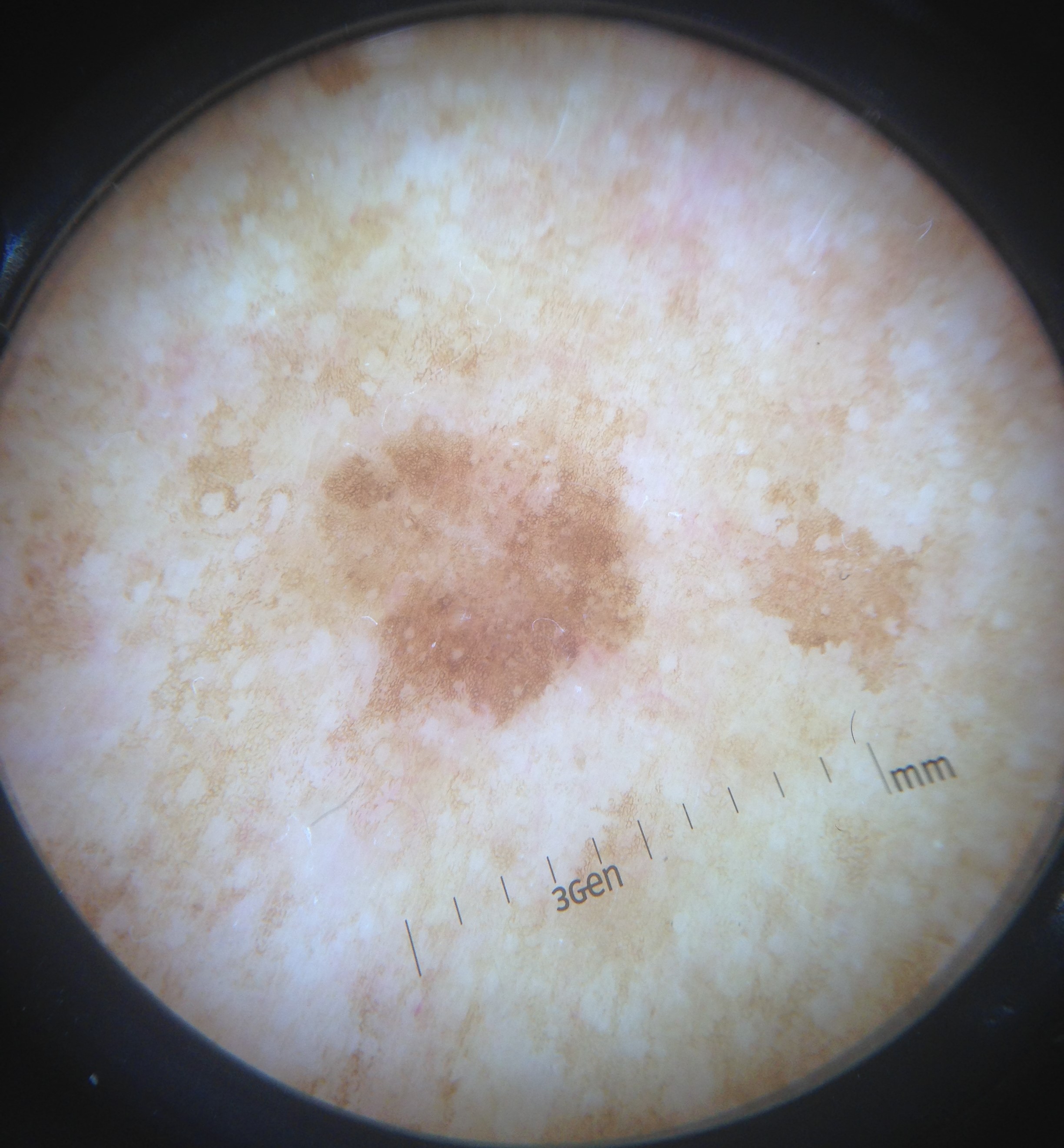| key | value |
|---|---|
| image type | dermoscopy |
| diagnosis | solar lentigo (expert consensus) |